Dermoscopy of a skin lesion:
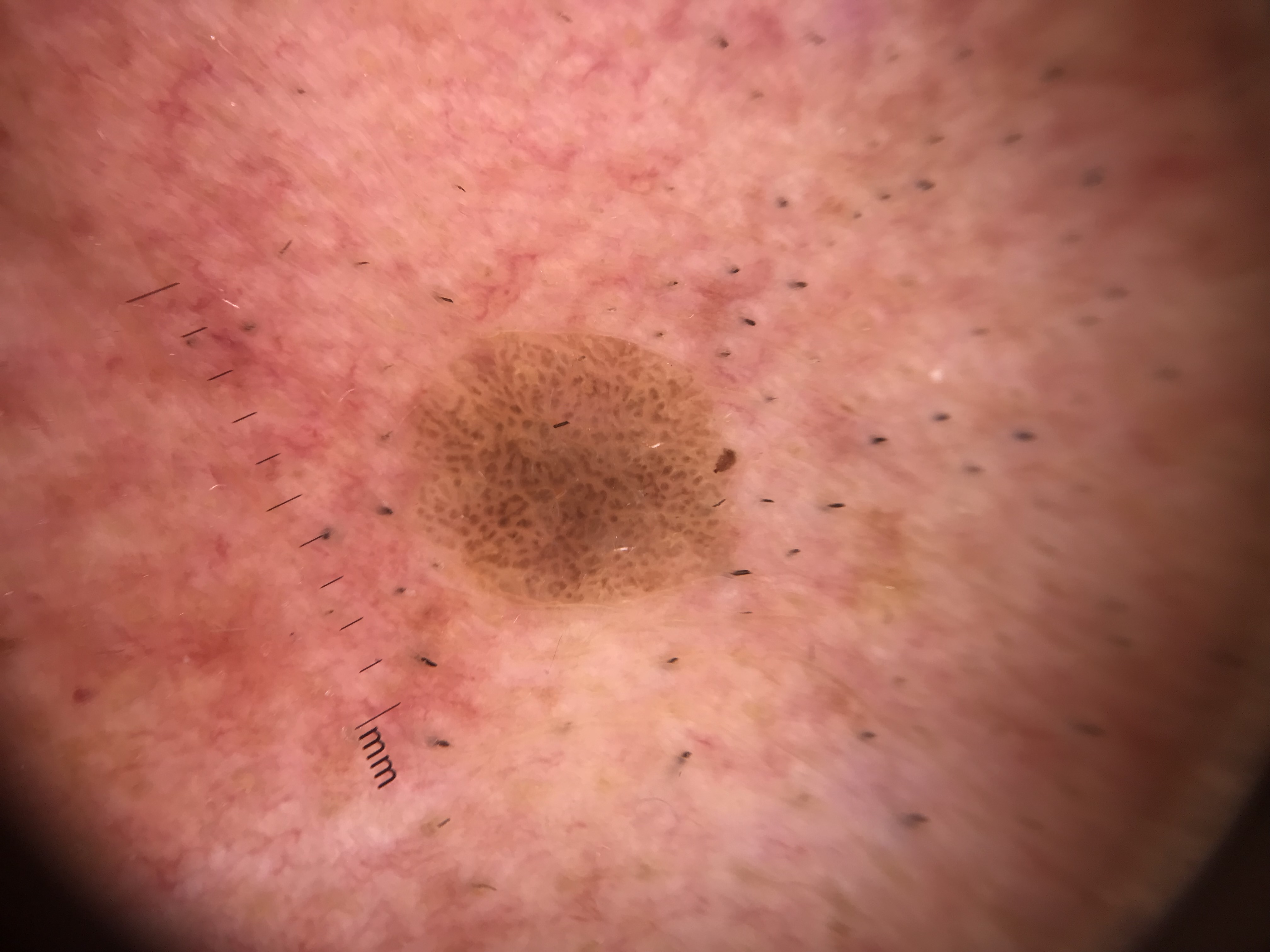The diagnostic label was a keratinocytic lesion — a seborrheic keratosis.